The photograph was taken at an angle. Symptoms reported: itching and bothersome appearance. Self-categorized by the patient as a rash. The contributor reports the lesion is raised or bumpy. Reported duration is one to four weeks. The lesion involves the back of the hand and arm. The contributor is a male aged 18–29: 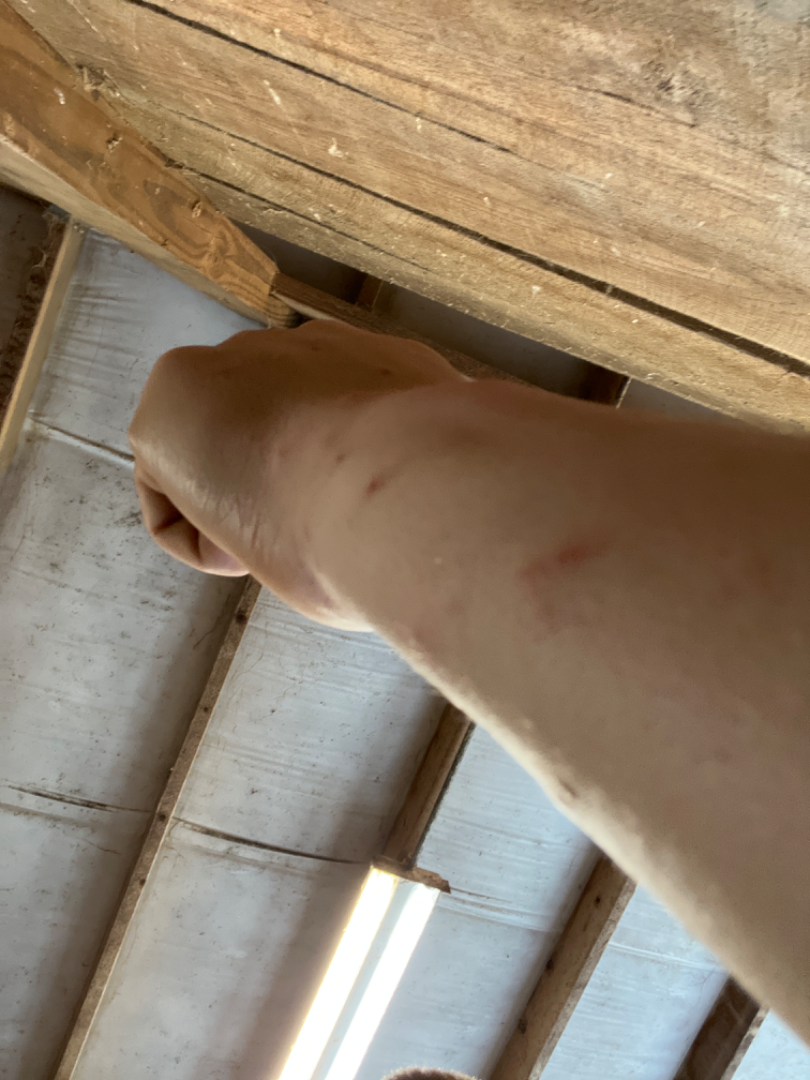assessment: ungradable on photographic review.